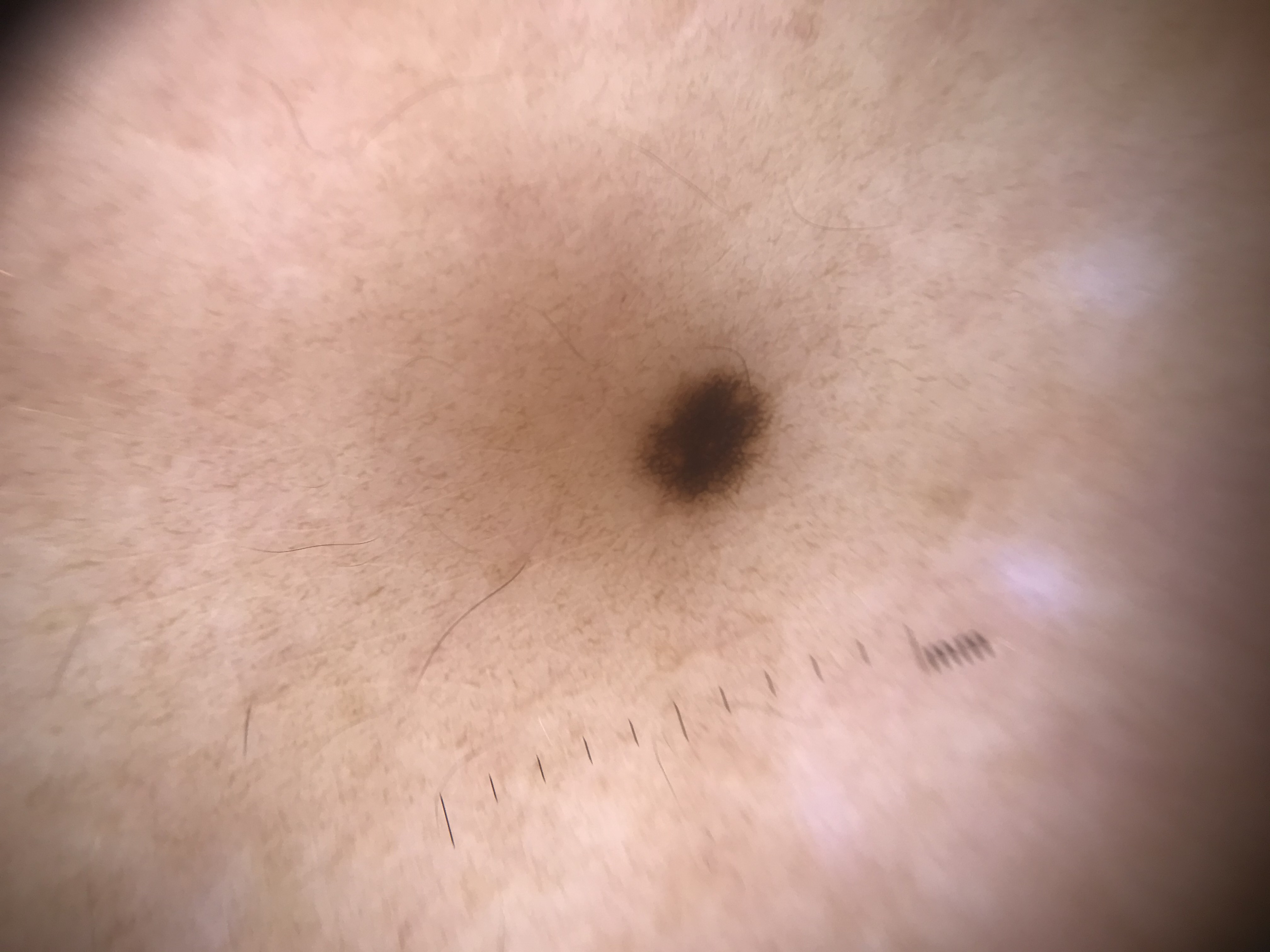assessment = junctional nevus (expert consensus).